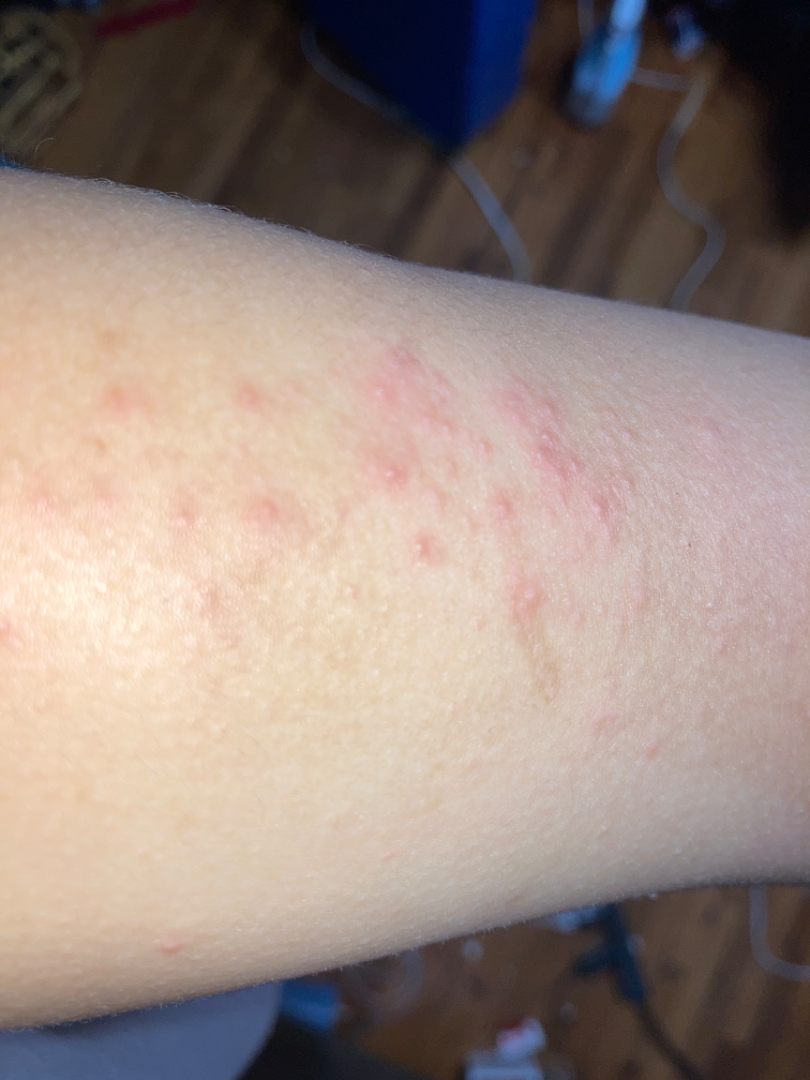The lesion is described as raised or bumpy.
The arm is involved.
The photograph is a close-up of the affected area.
Reported duration is less than one week.
Single-reviewer assessment: most consistent with Folliculitis; an alternative is Insect Bite; with consideration of Allergic Contact Dermatitis.